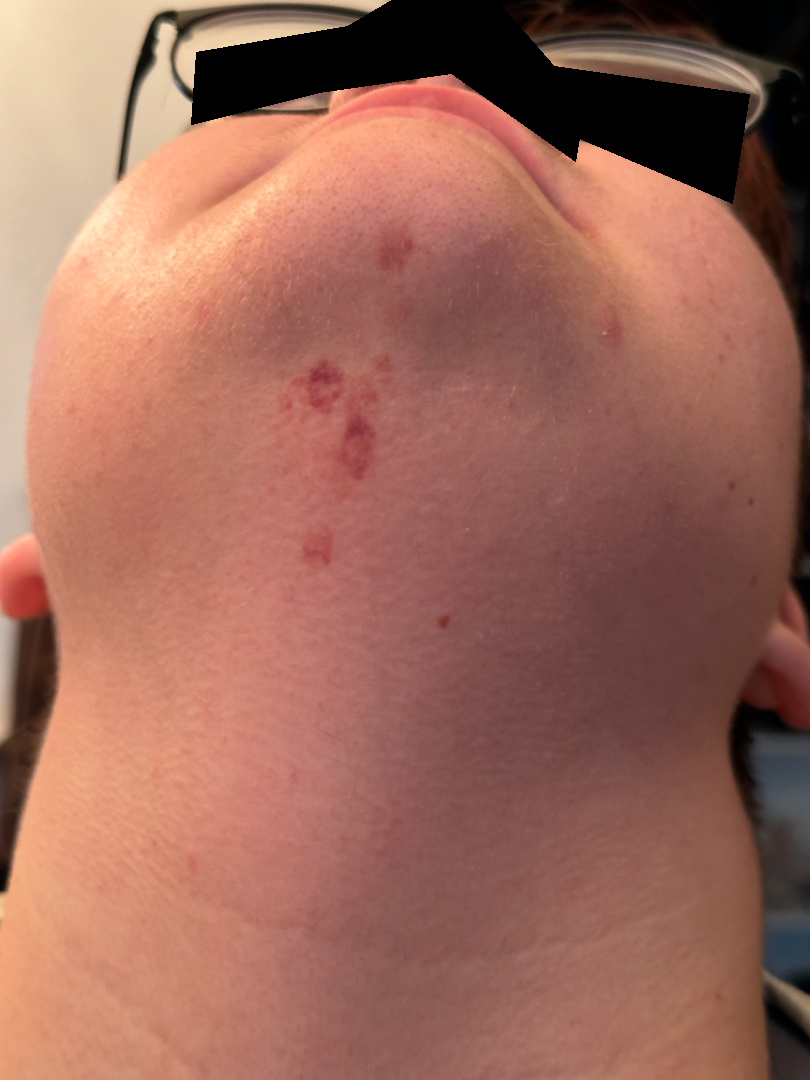The contributor notes the lesion is rough or flaky. No associated systemic symptoms reported. The patient did not report lesion symptoms. This is a close-up image. The leading consideration is Acne; also on the differential is Eruptive odontogenic cyst.